A dermoscopic photograph of a skin lesion.
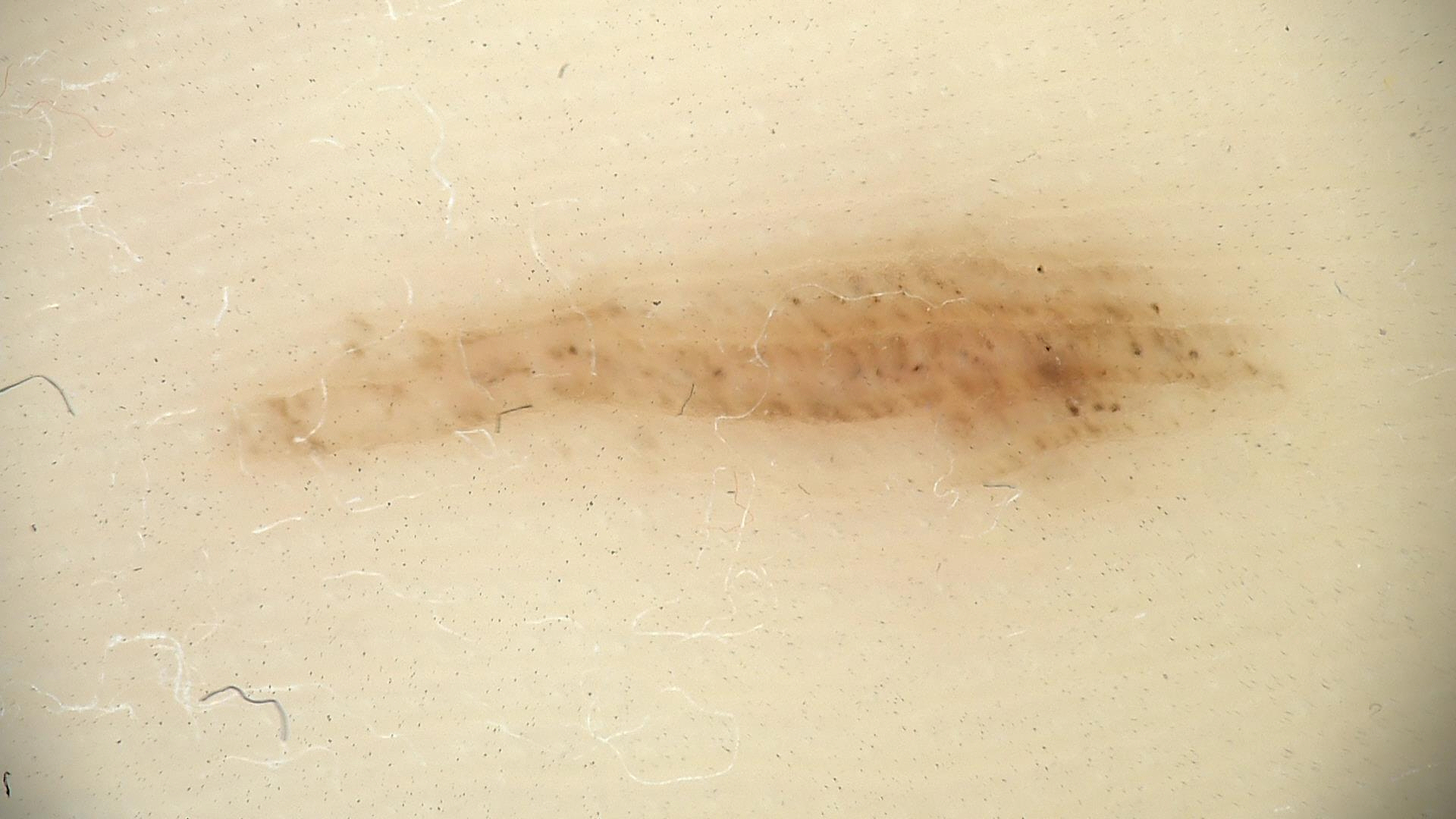diagnosis: acral dysplastic junctional nevus (expert consensus).